A dermatoscopic image of a skin lesion. A female patient, aged 68-72 — 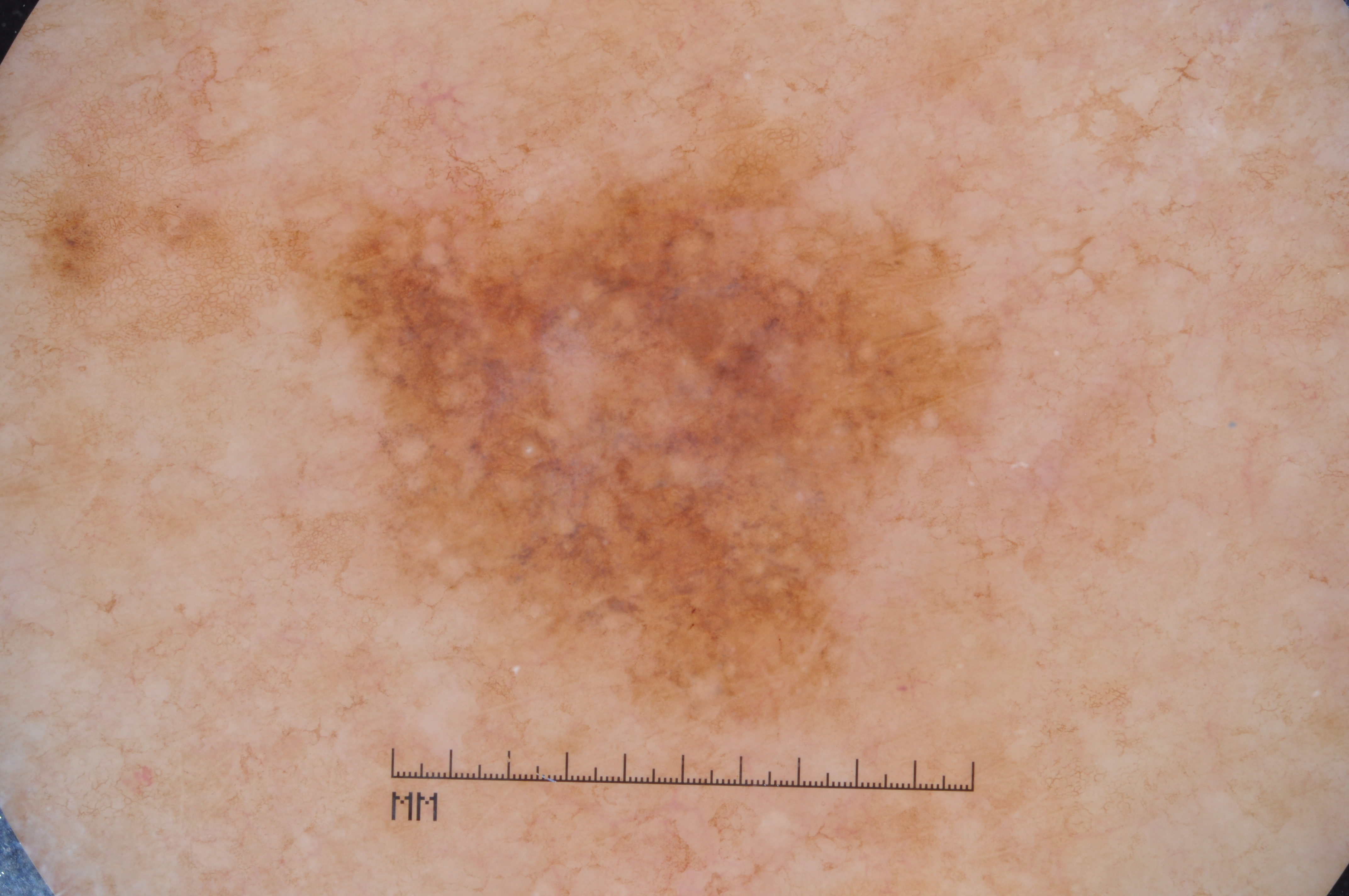{
  "lesion_location": {
    "bbox_xyxy": [
      306,
      133,
      991,
      714
    ]
  },
  "lesion_extent": "moderate",
  "dermoscopic_features": {
    "present": [
      "pigment network",
      "milia-like cysts"
    ],
    "absent": [
      "streaks",
      "negative network"
    ]
  },
  "diagnosis": {
    "name": "melanoma",
    "malignancy": "malignant",
    "lineage": "melanocytic",
    "provenance": "histopathology"
  }
}